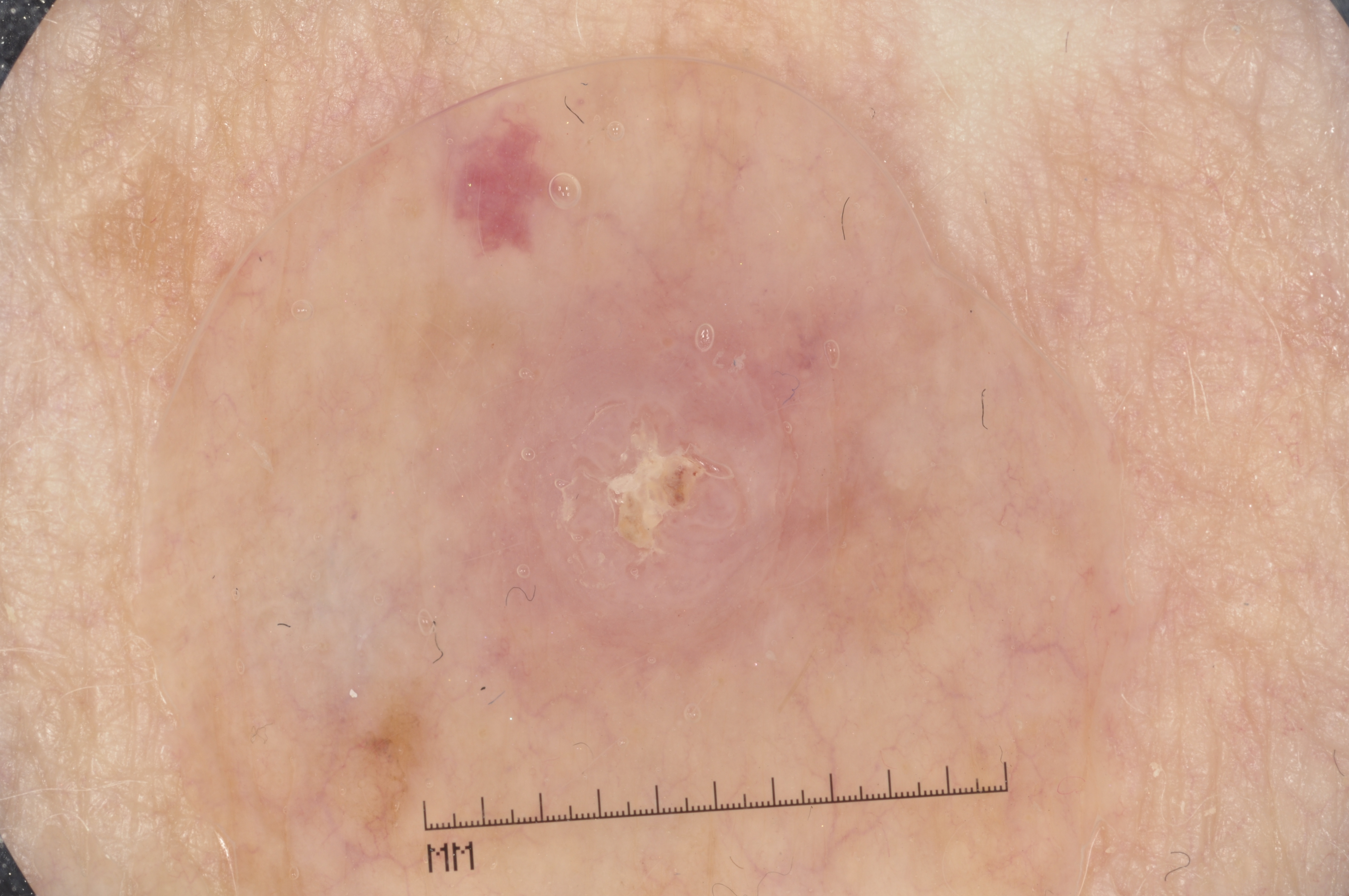A female subject, aged approximately 75. This is a dermoscopic photograph of a skin lesion. As (left, top, right, bottom), the visible lesion spans (393, 270, 935, 721). Dermoscopic review identifies no pigment network, streaks, milia-like cysts, or negative network. The lesion takes up about 14% of the image. Diagnosed as a seborrheic keratosis, a lesion of keratinocytic origin.